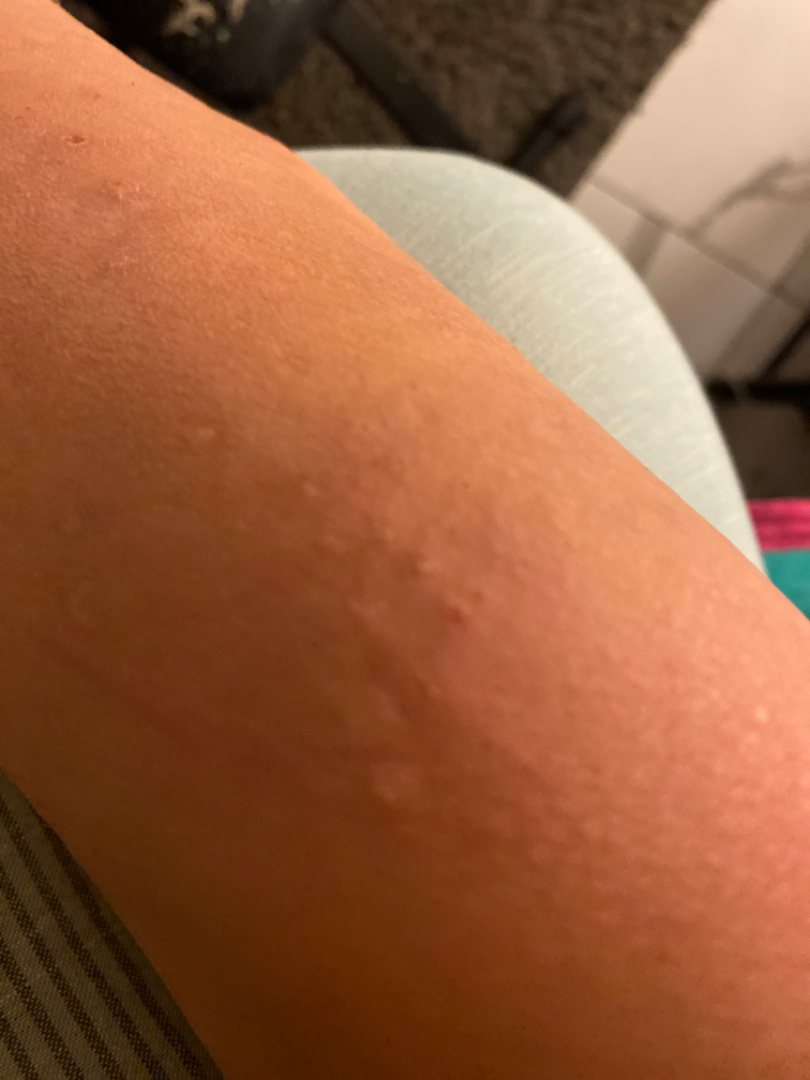Patient information: The patient is a female aged 40–49. This is a close-up image. Located on the front of the torso and arm. Review: The reviewing dermatologists' impression was: Folliculitis (weight 0.35); Tinea (weight 0.22); Eczema (weight 0.22); Lichen Simplex Chronicus (weight 0.22).